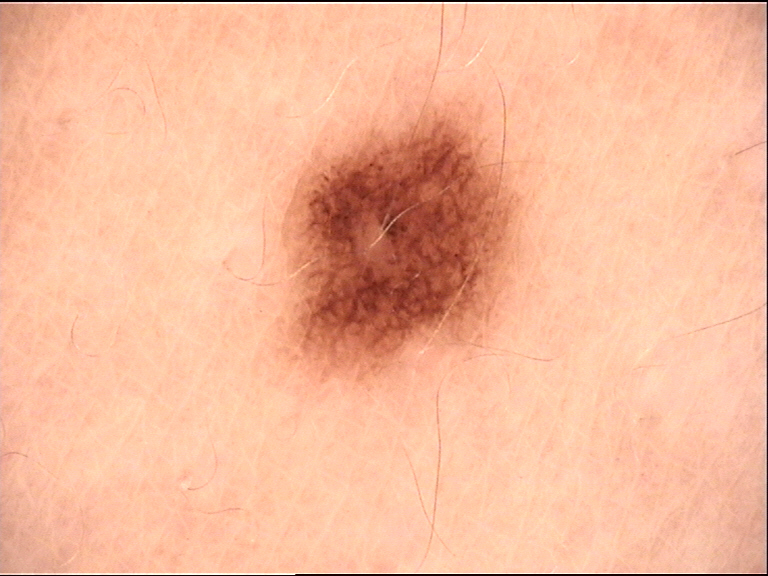label: junctional nevus (expert consensus)